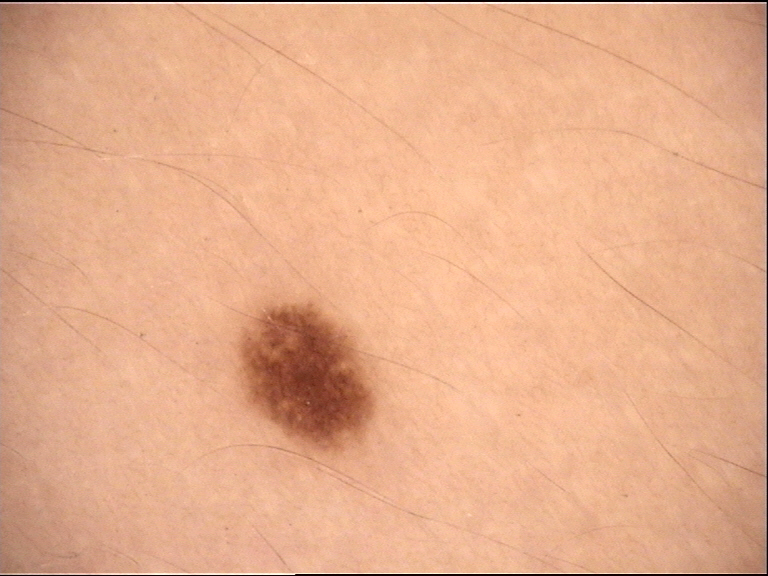Case:
A dermatoscopic image of a skin lesion.
Impression:
Labeled as a banal lesion — a junctional nevus.